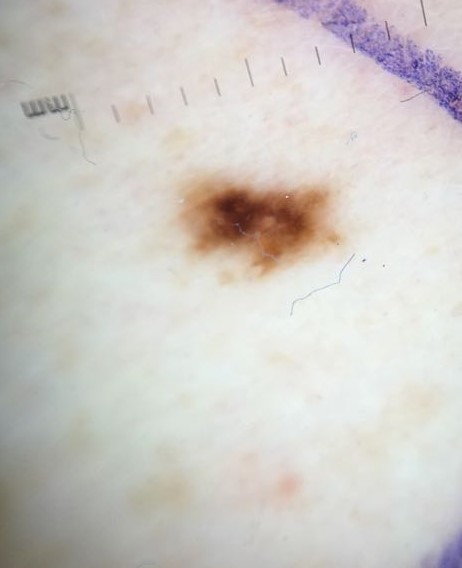Case:
– label: dysplastic junctional nevus (expert consensus)